A dermoscopic image of a skin lesion.
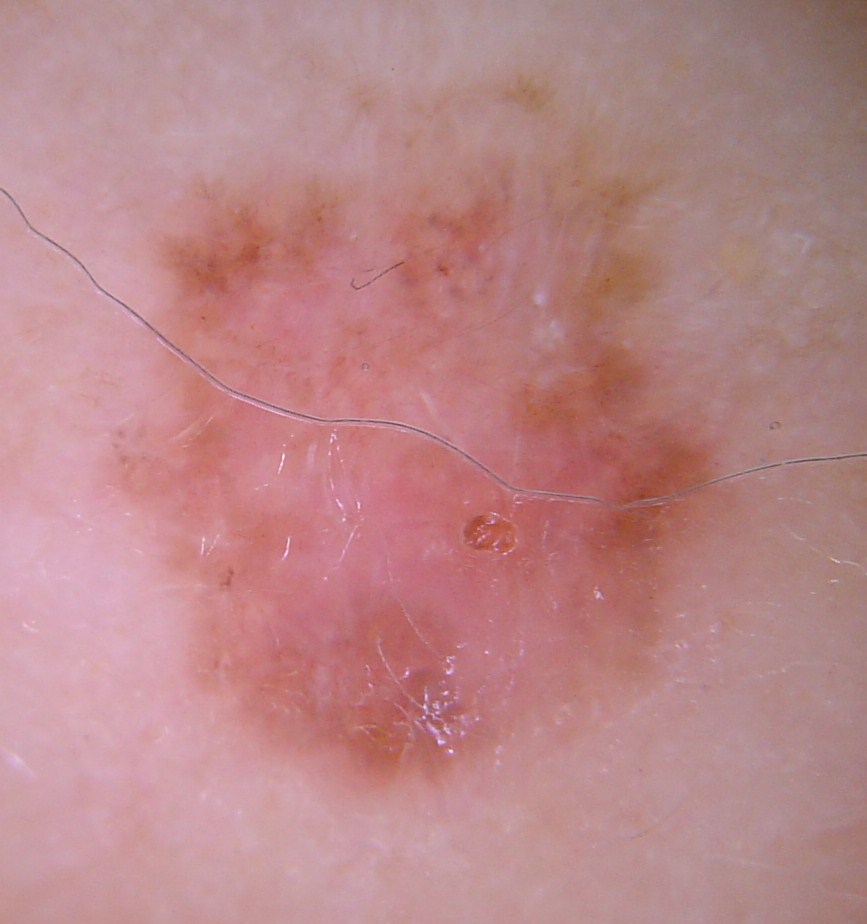Q: What is the lesion category?
A: keratinocytic
Q: What is this lesion?
A: basal cell carcinoma (biopsy-proven)